This is a close-up image · FST VI; human graders estimated MST 7–8 — 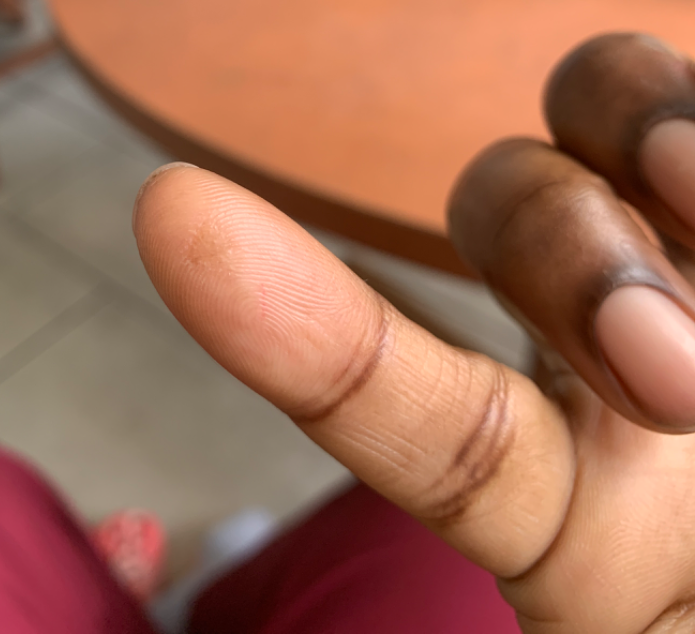Diagnostic features were not clearly distinguishable in this photograph.